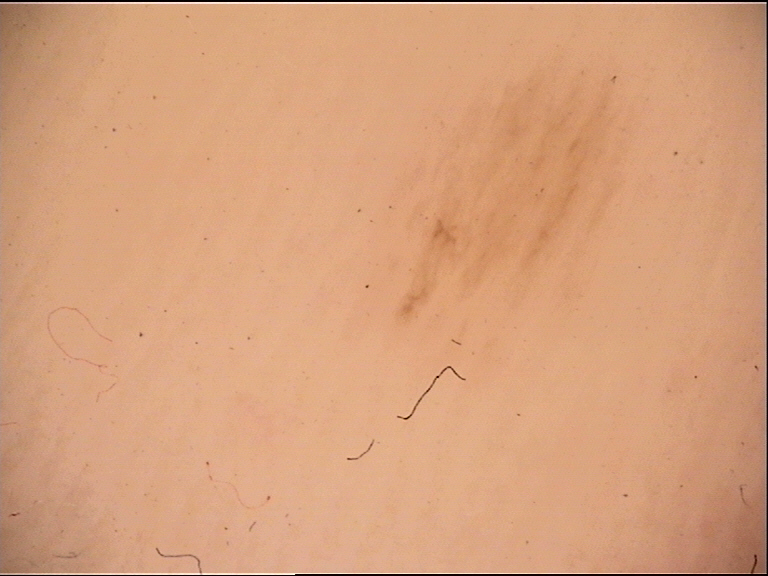A dermoscopic photograph of a skin lesion. This is a banal lesion. Labeled as an acral junctional nevus.